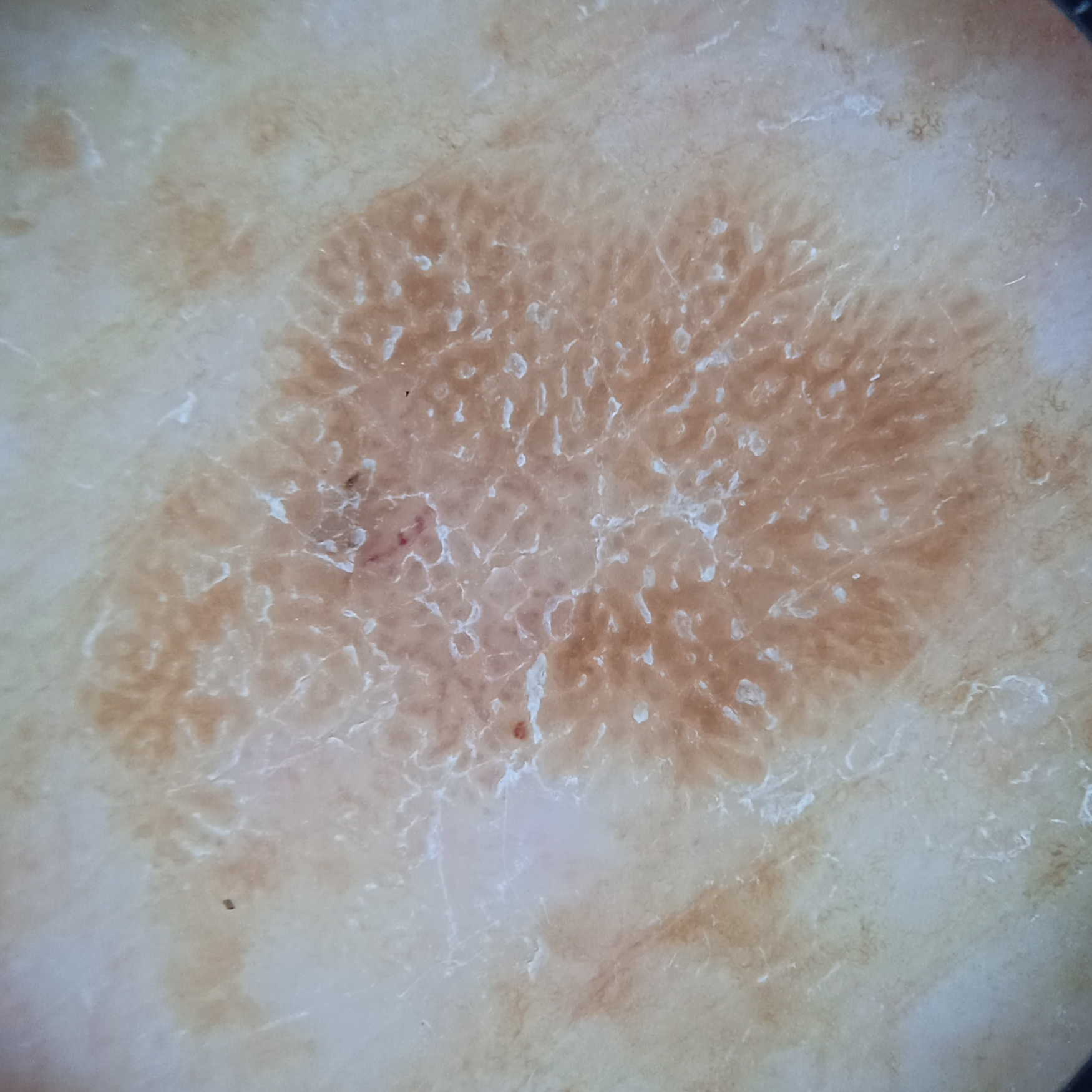Clinical context:
Imaged for a research study, with no referral diagnosis recorded. A male patient 73 years of age. The lesion involves the back. The lesion measures approximately 10.7 mm.
Impression:
The consensus diagnosis for this lesion was a seborrheic keratosis.